A dermoscopy image of a single skin lesion · the patient is a female in their mid-50s.
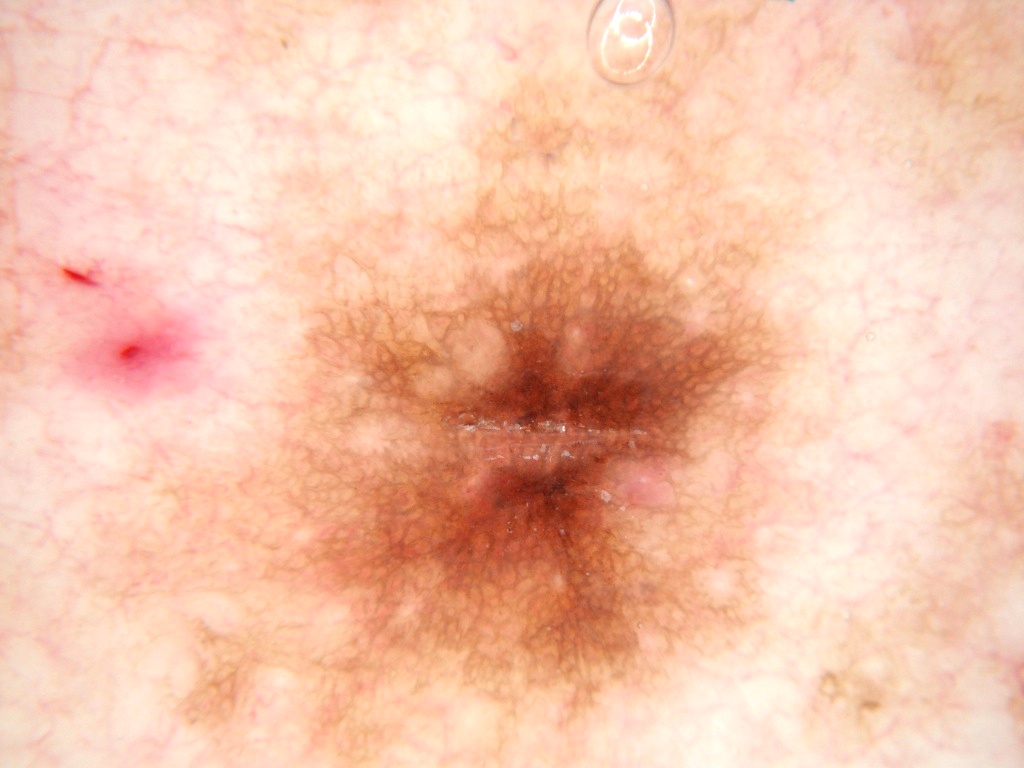The lesion takes up a large portion of the image.
Lesion location: left=97, top=0, right=805, bottom=763.
The lesion is clipped by the edge of the image.
On dermoscopy, the lesion shows pigment network and milia-like cysts; no globules, streaks, or negative network.
Consistent with a melanocytic nevus, a benign lesion.